A skin lesion imaged with a dermatoscope:
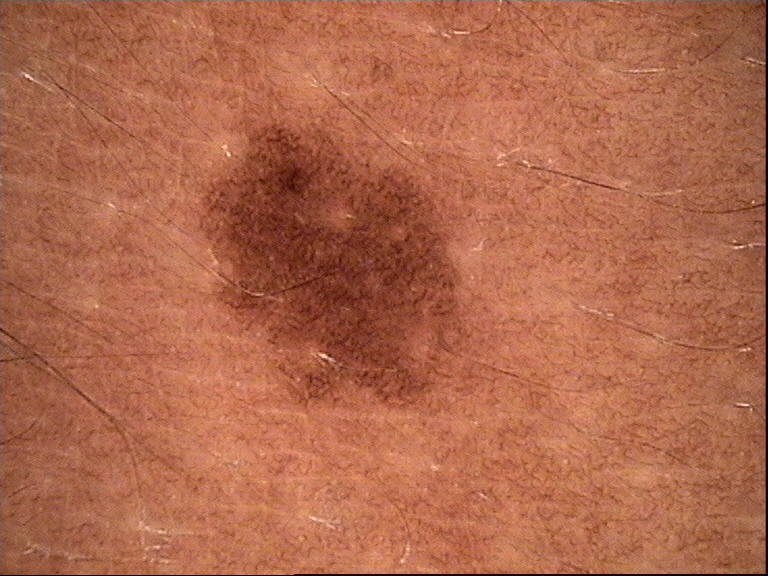diagnosis: dysplastic junctional nevus (expert consensus).